The patient reports no sunbed use · a macroscopic clinical photograph of a skin lesion · the patient says their skin reddens painfully with sun exposure · collected as part of a research study, without a referral diagnosis · the patient describes having a moderate number of moles · a female subject 81 years of age — 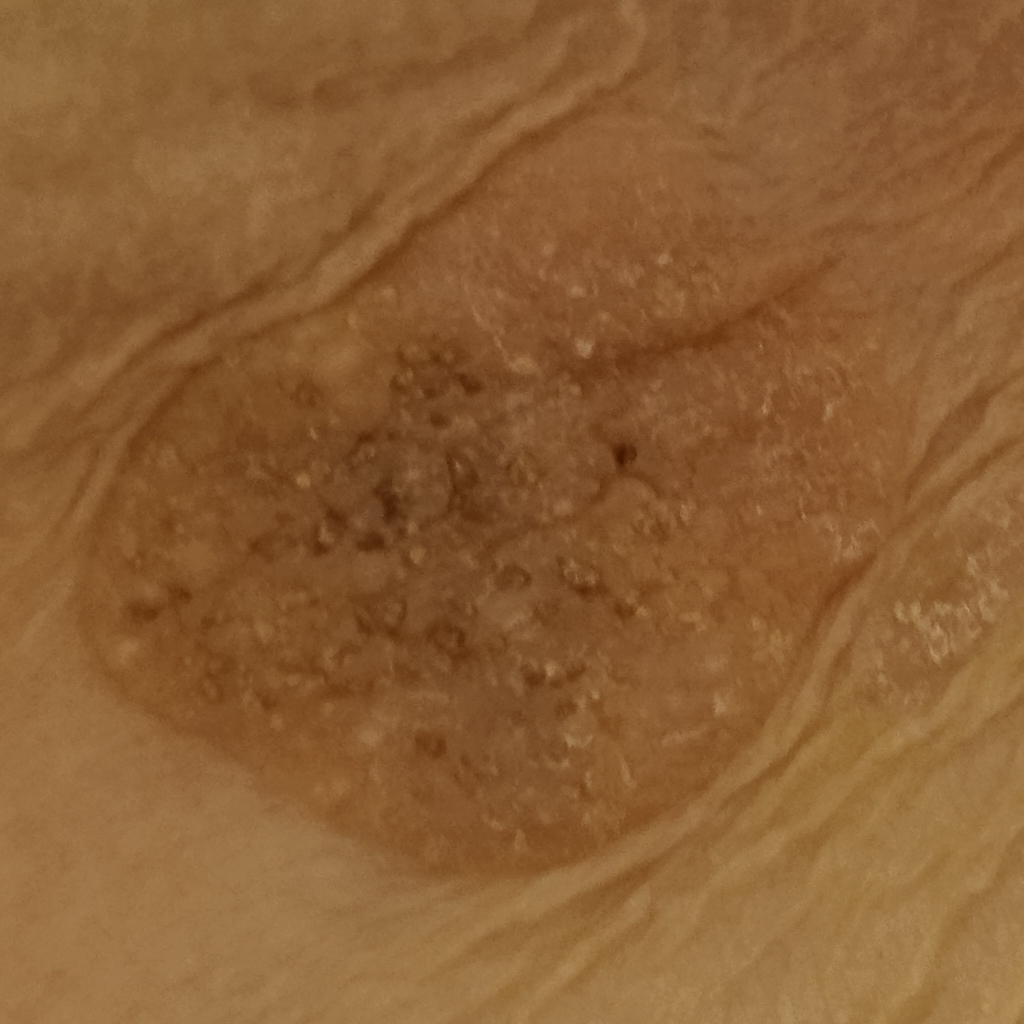Located on the torso. The lesion is about 31 mm across. The dermatologists' assessment was a seborrheic keratosis.